A dermoscopic photograph of a skin lesion:
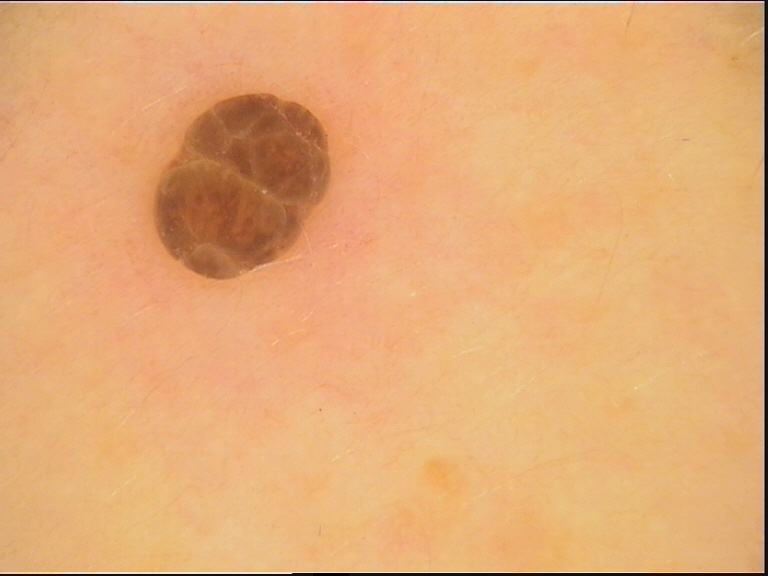Case: The architecture is that of a banal lesion. Impression: Labeled as a dermal nevus.